Male subject, age 40–49 · the lesion involves the back of the hand · this is a close-up image — 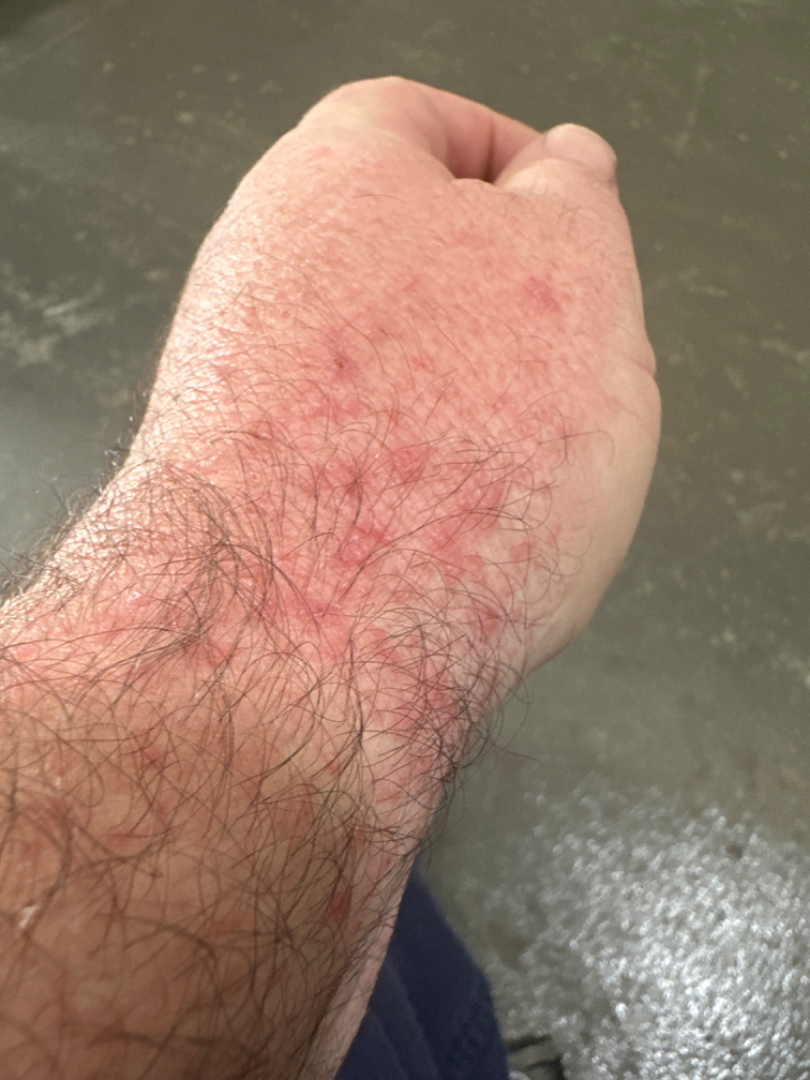Skin tone: Fitzpatrick I. The condition has been present for less than one week. The lesion is described as raised or bumpy. The lesion is associated with itching. No constitutional symptoms were reported. The patient described the issue as a rash. On remote dermatologist review: the impression was split between Folliculitis, Eczema and Allergic Contact Dermatitis.